A male patient, aged around 60; a dermoscopy image of a single skin lesion:
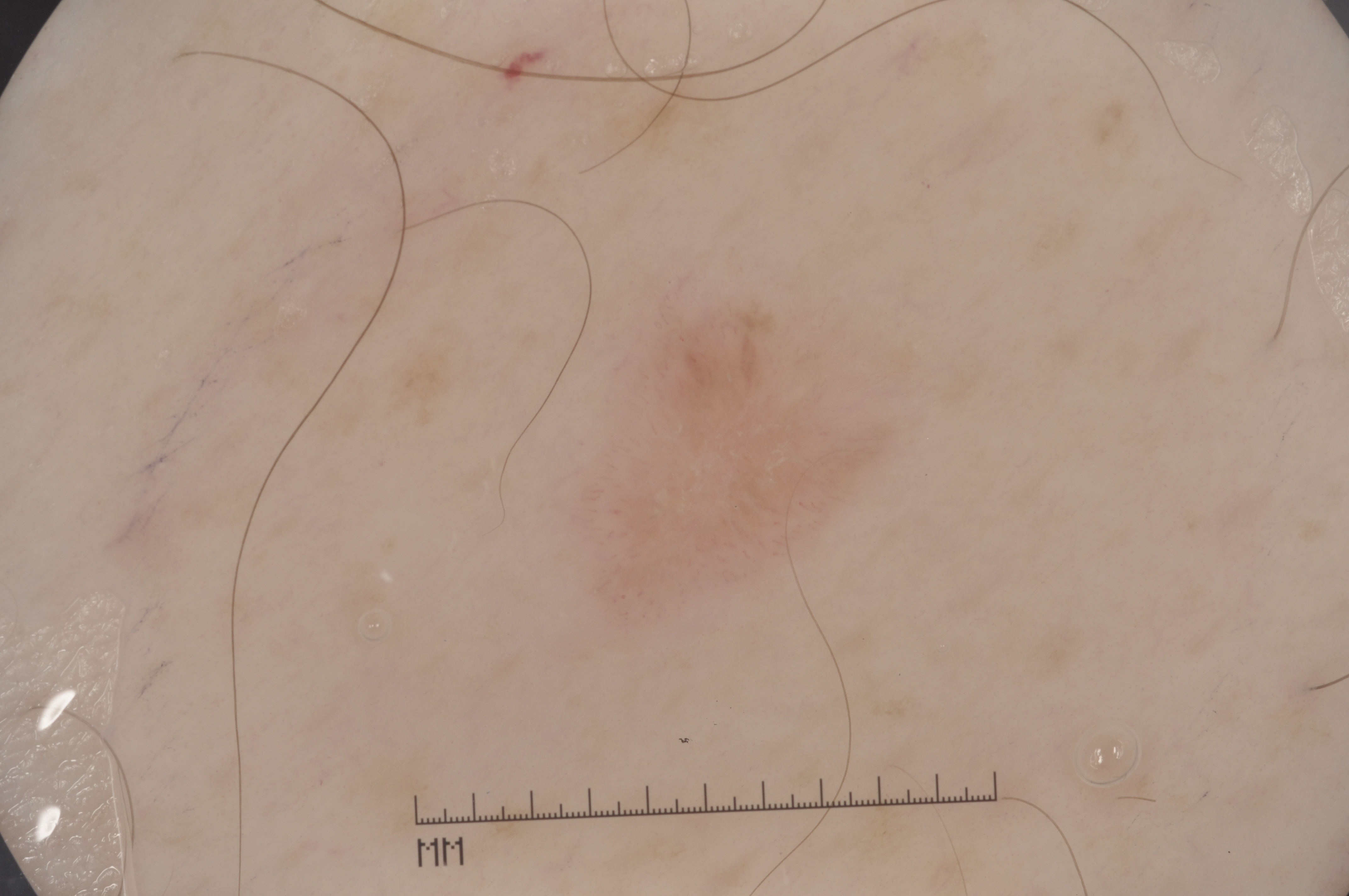bounding box = box(580, 309, 885, 616); absent dermoscopic findings = streaks, pigment network, negative network, and milia-like cysts; assessment = a seborrheic keratosis, a benign skin lesion.